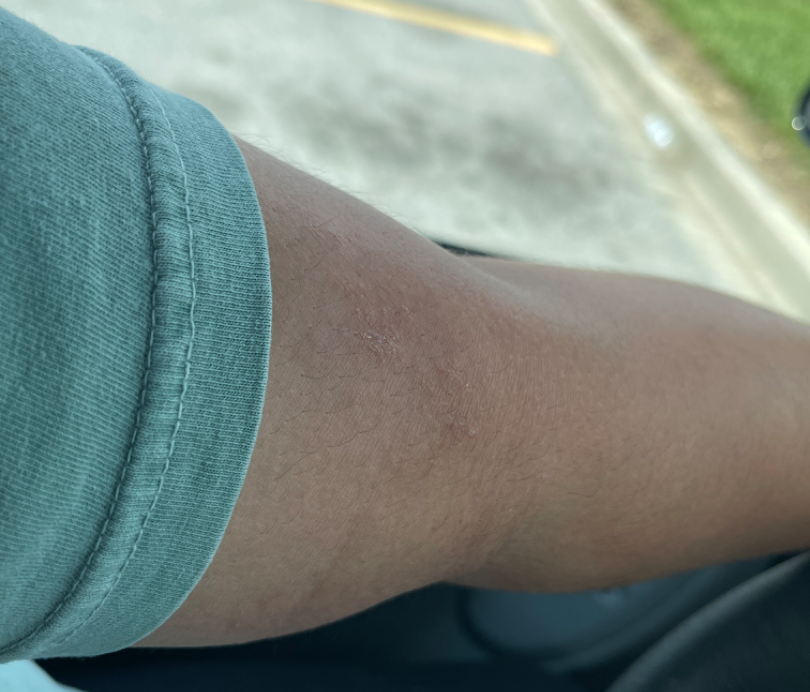photo taken = at a distance
differential diagnosis = the impression on review was Acute and chronic dermatitis